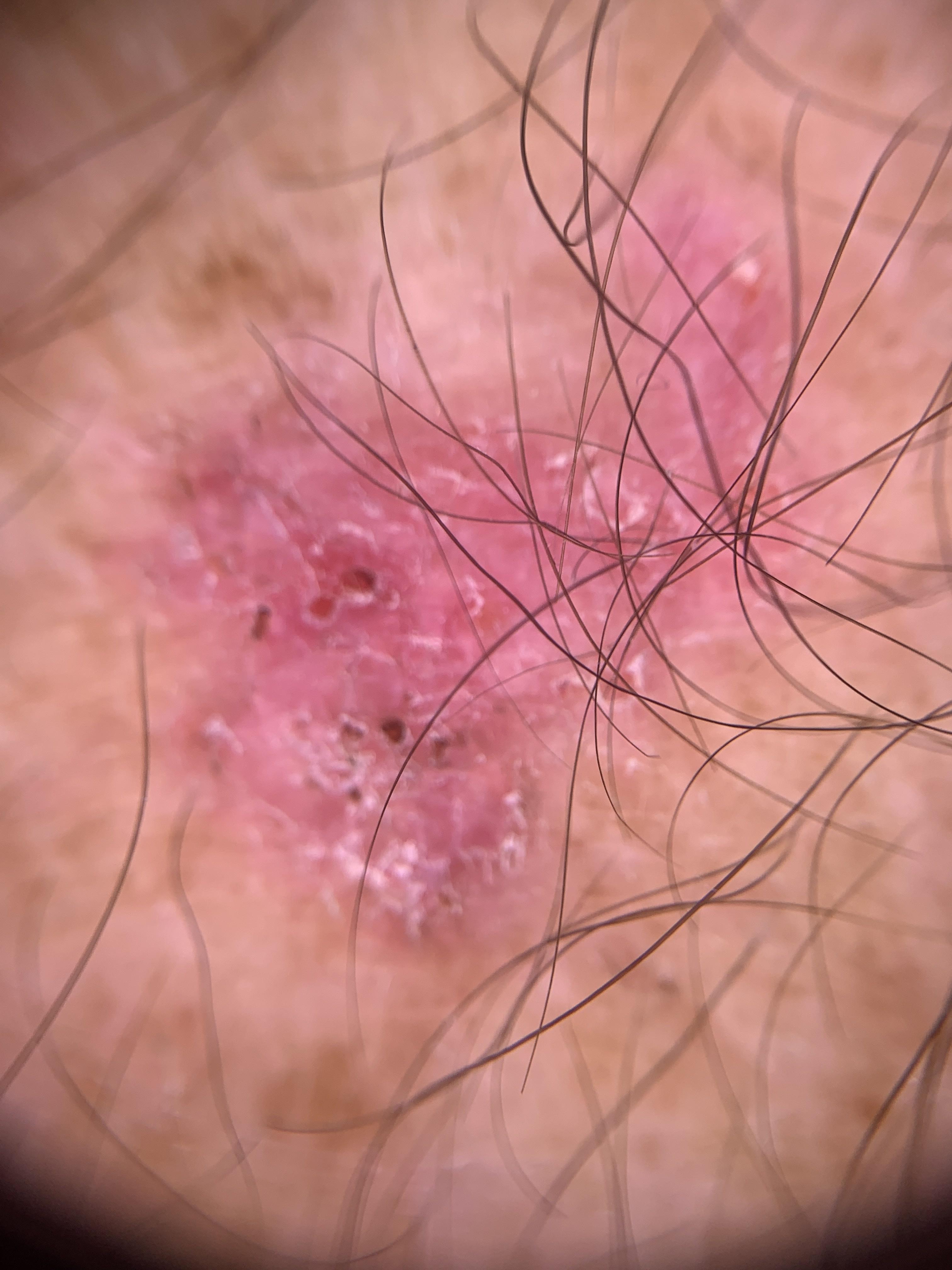<skin_lesion>
<skin_type>II</skin_type>
<image>contact-polarized dermoscopy</image>
<melanoma_history>
<personal_hx_melanoma>true</personal_hx_melanoma>
</melanoma_history>
<patient>
<age_approx>80</age_approx>
<sex>male</sex>
</patient>
<diagnosis>
<name>Basal cell carcinoma</name>
<malignancy>malignant</malignancy>
<confirmation>histopathology</confirmation>
<lineage>adnexal</lineage>
</diagnosis>
</skin_lesion>